Dermoscopy of a skin lesion: 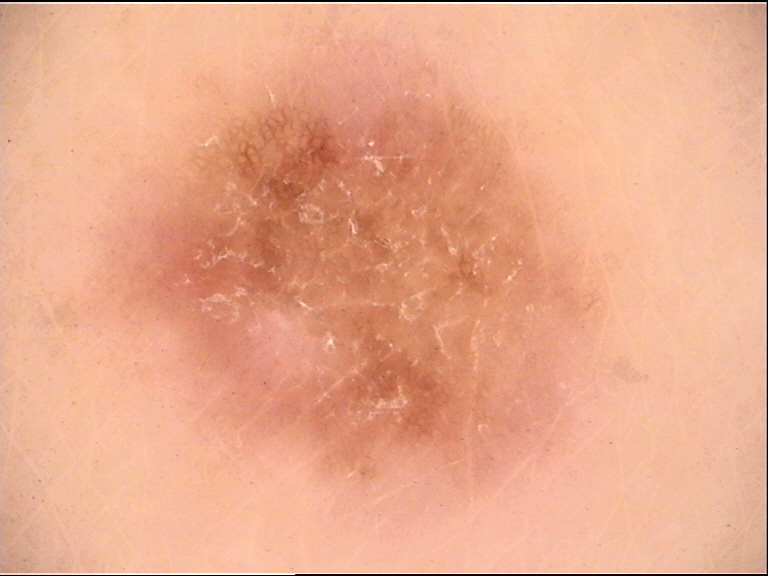Diagnosed as a benign lesion — a dysplastic junctional nevus.